A female patient aged 73 · a clinical close-up photograph of a skin lesion.
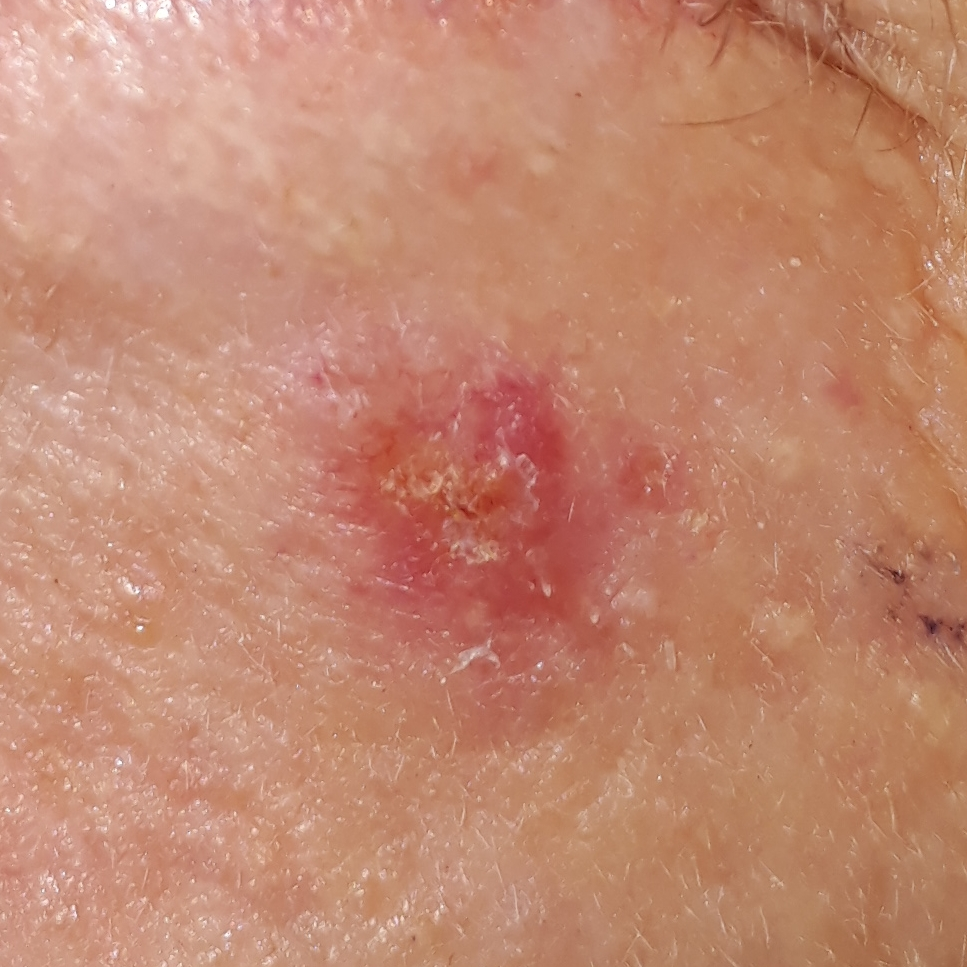The lesion is on the face.
By the patient's account, the lesion is elevated and itches, but does not hurt.
The biopsy diagnosis was a basal cell carcinoma.